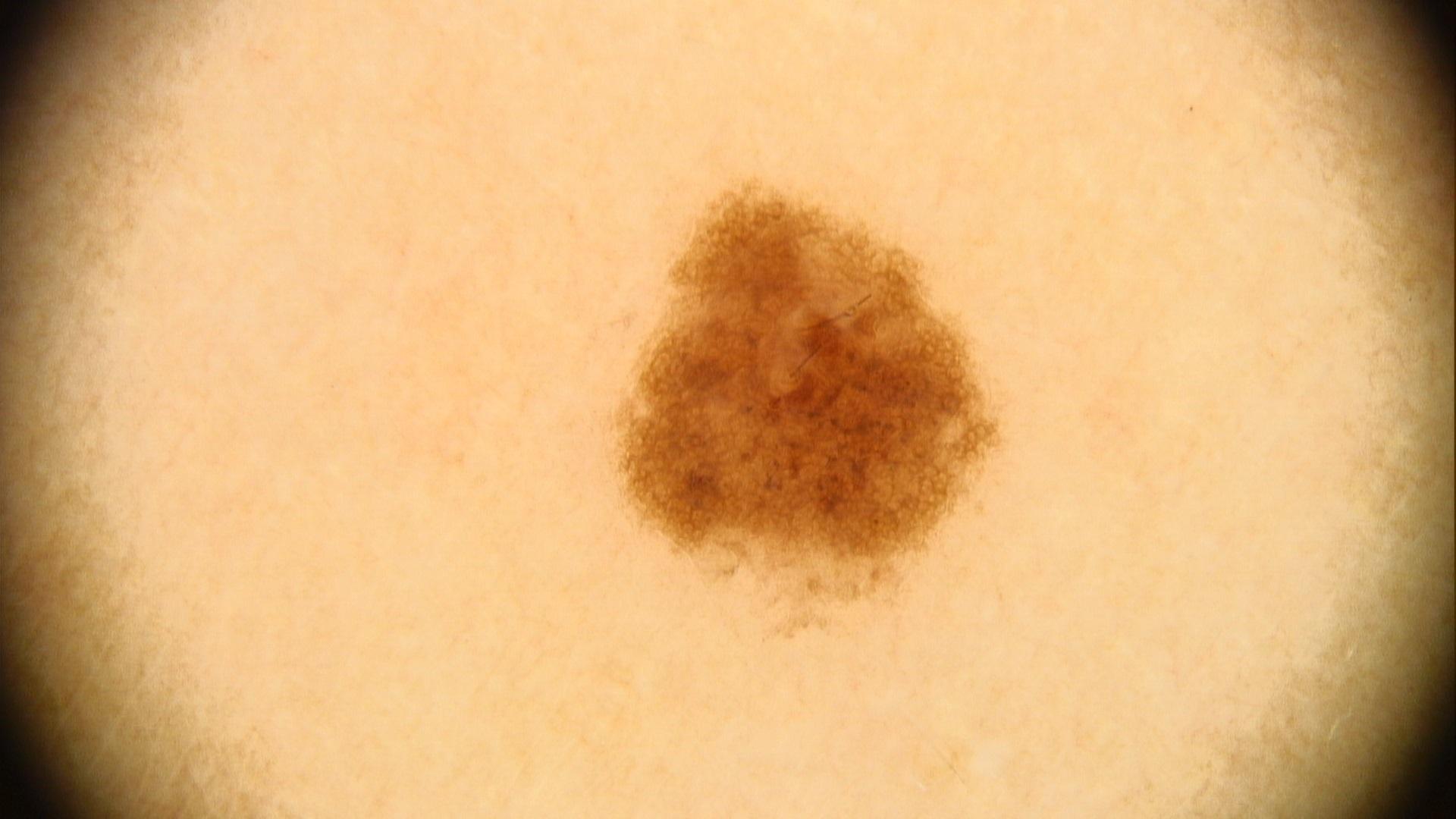  diagnosis:
    name: Nevus
    malignancy: benign
    confirmation: expert clinical impression
    lineage: melanocytic